A skin lesion imaged with a dermatoscope. A female patient aged around 70 — 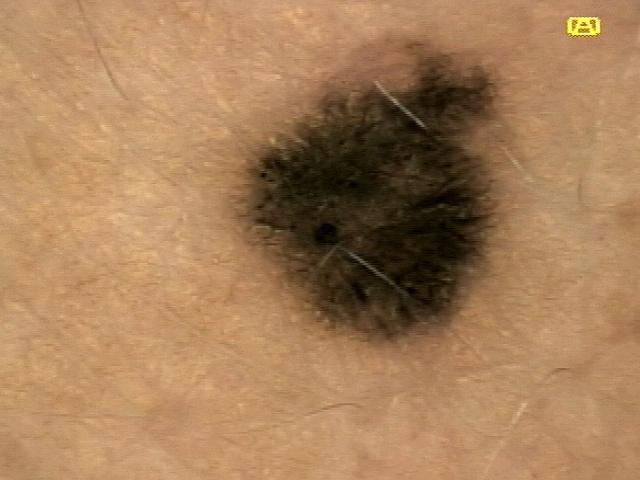The lesion is located on the trunk. The biopsy diagnosis was a nevus.